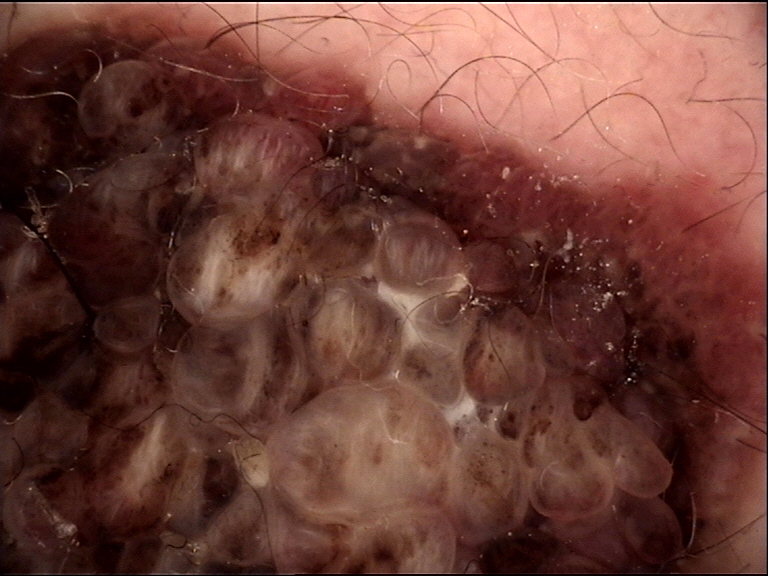{
  "image": "dermoscopy",
  "diagnosis": {
    "name": "congenital compound nevus",
    "code": "ccb",
    "malignancy": "benign",
    "super_class": "melanocytic",
    "confirmation": "expert consensus"
  }
}